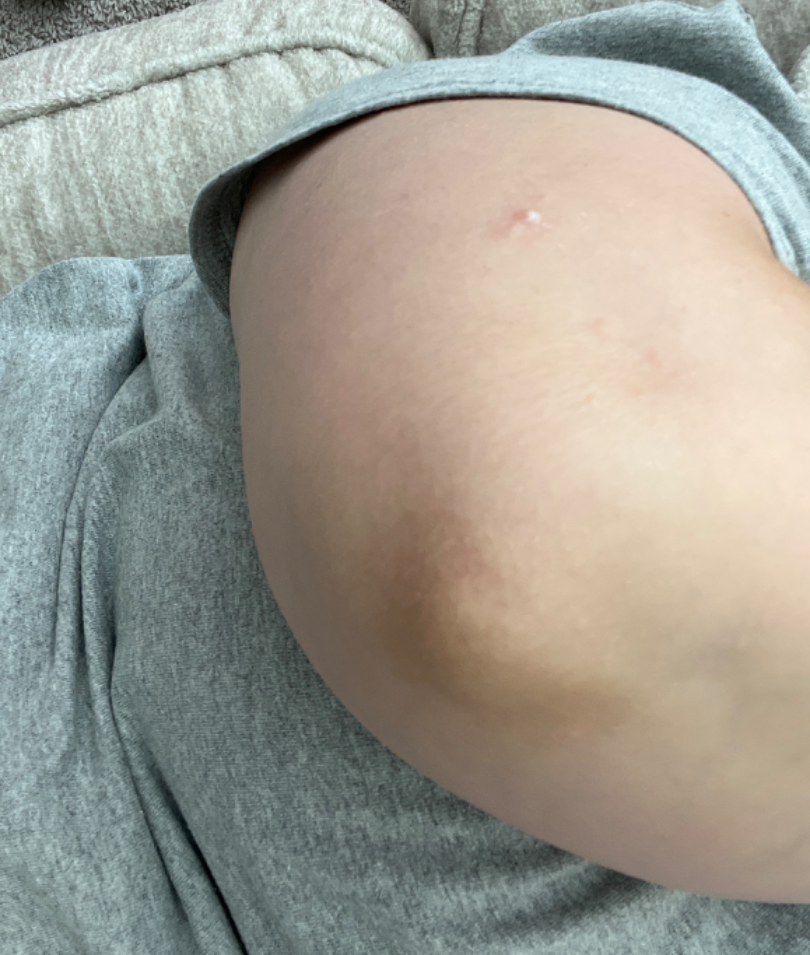The case was indeterminate on photographic review. The lesion involves the arm. This image was taken at a distance.